Close-up view.
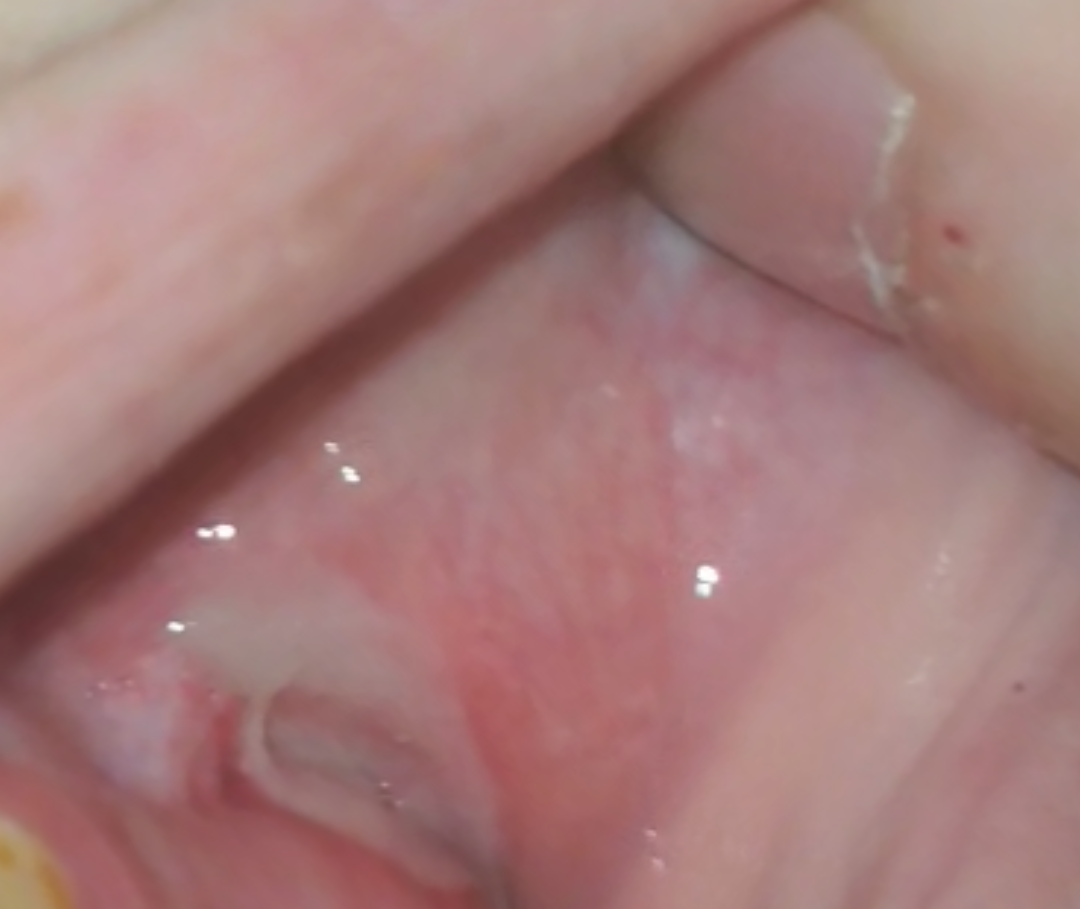Diagnostic features were not clearly distinguishable in this photograph.